The lesion involves the leg and arm · the patient described the issue as a rash · the lesion is described as flat · the photo was captured at an angle · reported duration is less than one week · lay graders estimated Monk Skin Tone 3 (US pool) or 2 (India pool) · the lesion is associated with itching, burning, enlargement and bothersome appearance — 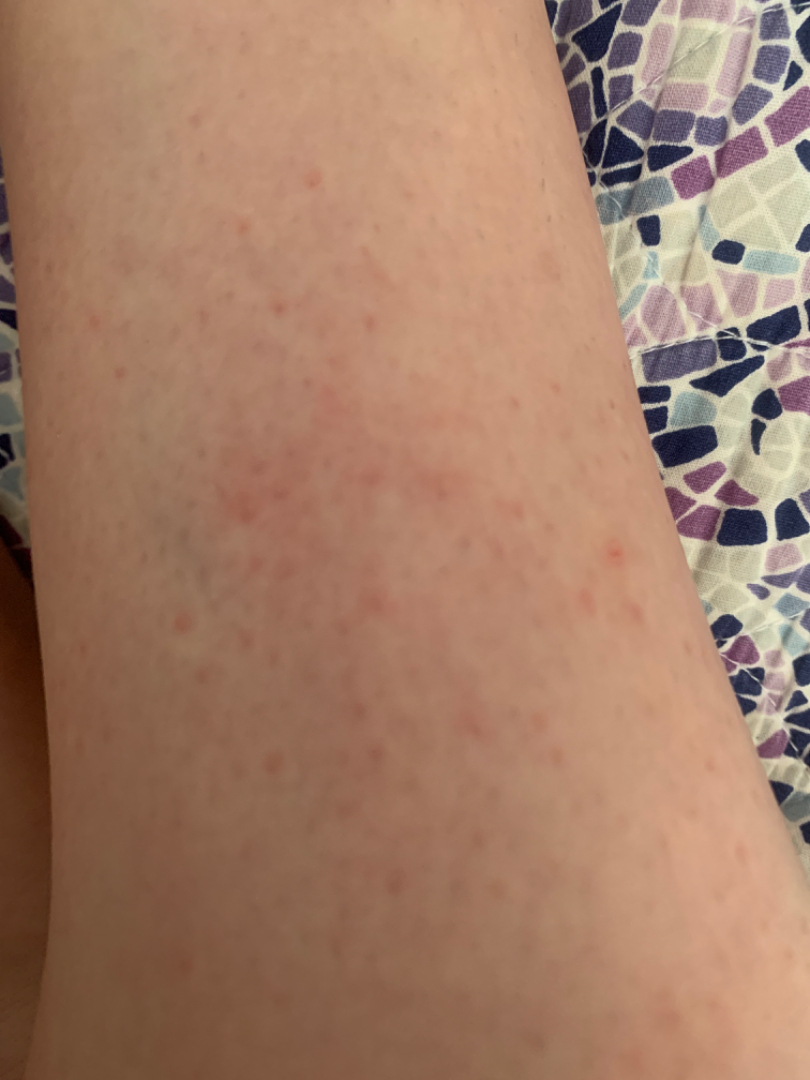{"assessment": "unable to determine"}